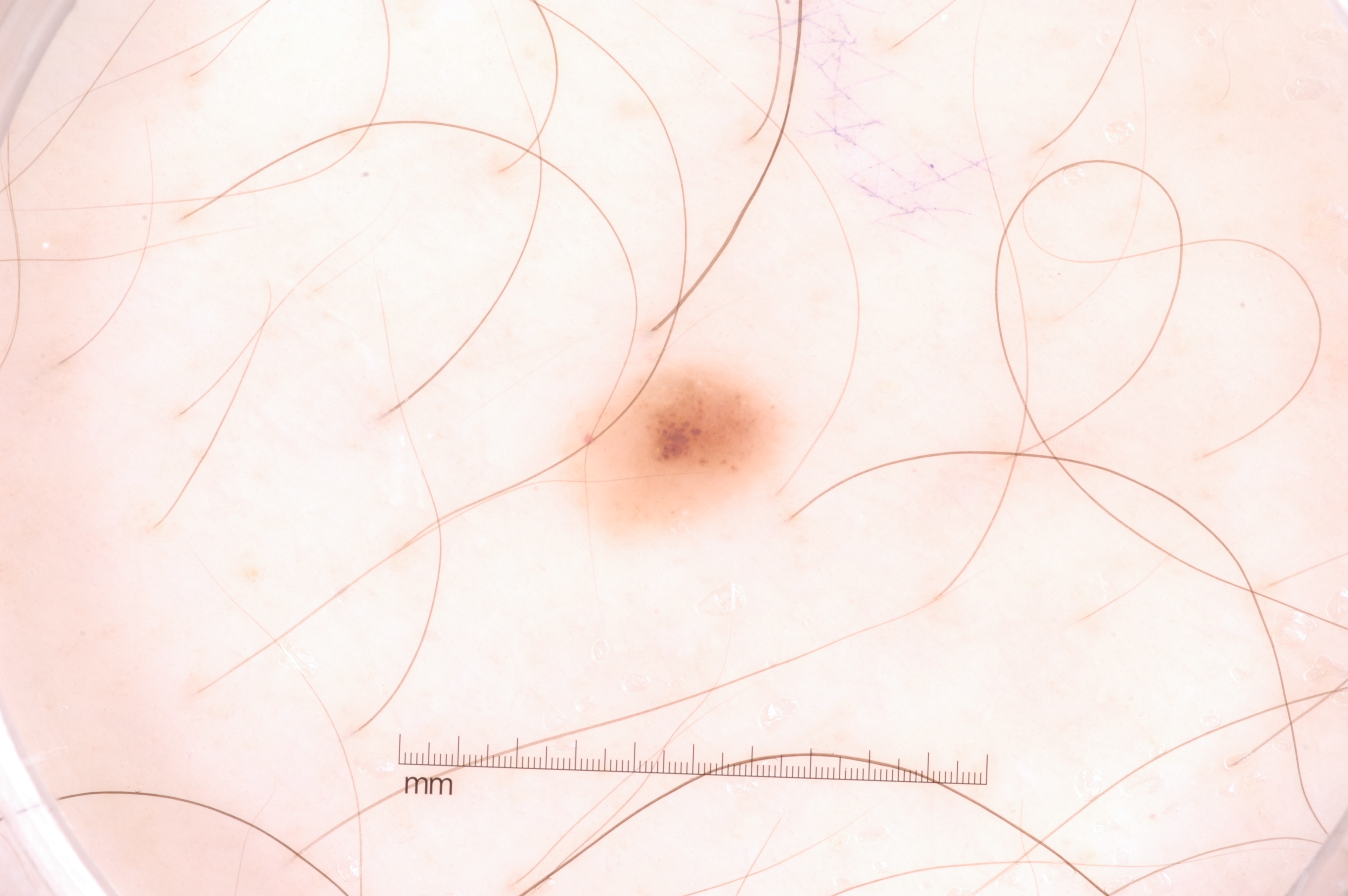A skin lesion imaged with a dermatoscope.
With coordinates (x1, y1, x2, y2), lesion location: box(560, 359, 792, 551).
Dermoscopically, the lesion shows no pigment network, milia-like cysts, streaks, or negative network.
The lesion is small relative to the field of view.
The diagnostic assessment was a melanocytic nevus.